The arm is involved. Male patient, age 30–39. The lesion is described as rough or flaky and raised or bumpy. The patient described the issue as a rash. This is a close-up image. Present for one to four weeks:
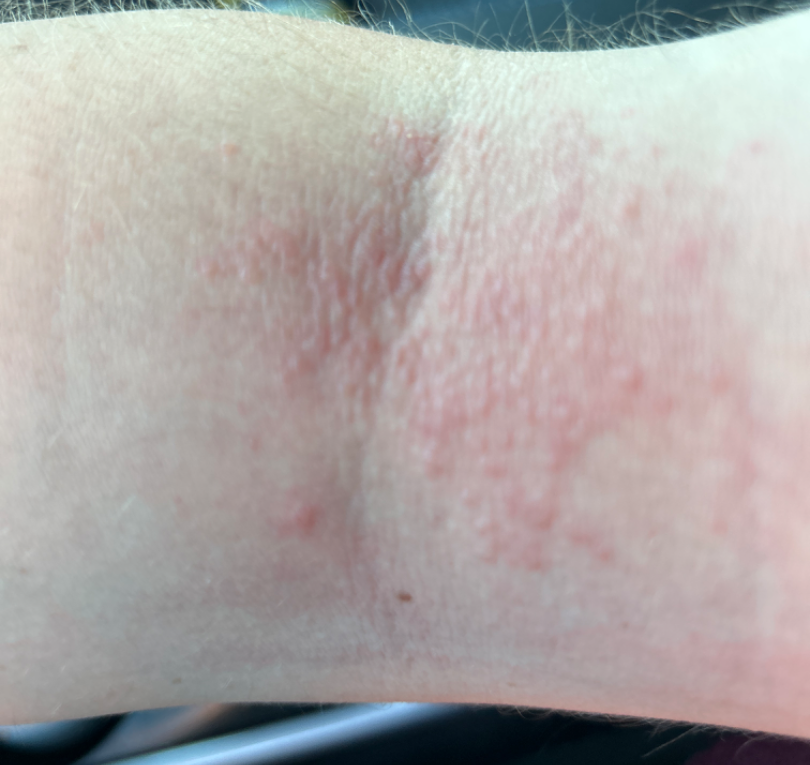| feature | finding |
|---|---|
| differential diagnosis | in keeping with Eczema |